A clinical photograph of a skin lesion; few moles overall by the patient's own estimate; collected as part of a research study, without a referral diagnosis.
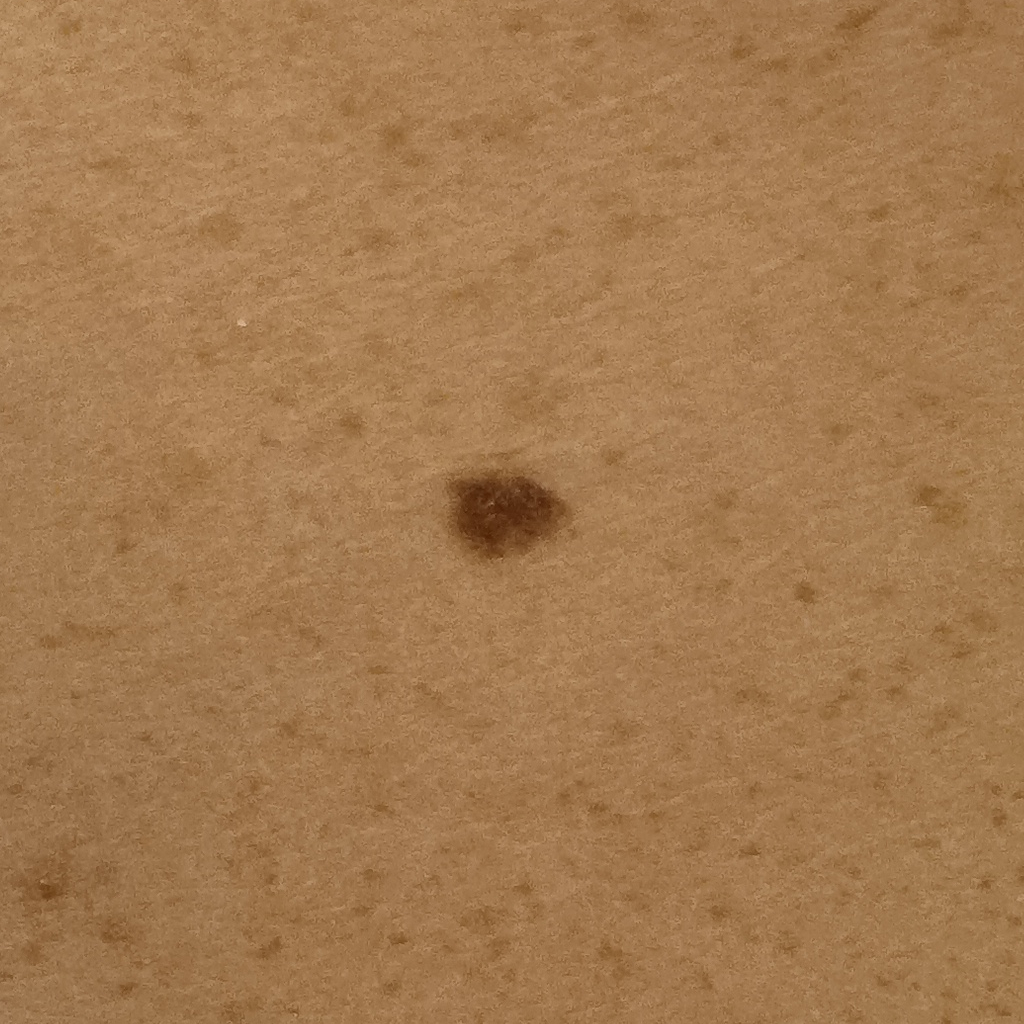Findings:
• diameter — 5.6 mm
• diagnostic label — melanocytic nevus (dermatologist consensus)